A dermoscopy image of a single skin lesion: 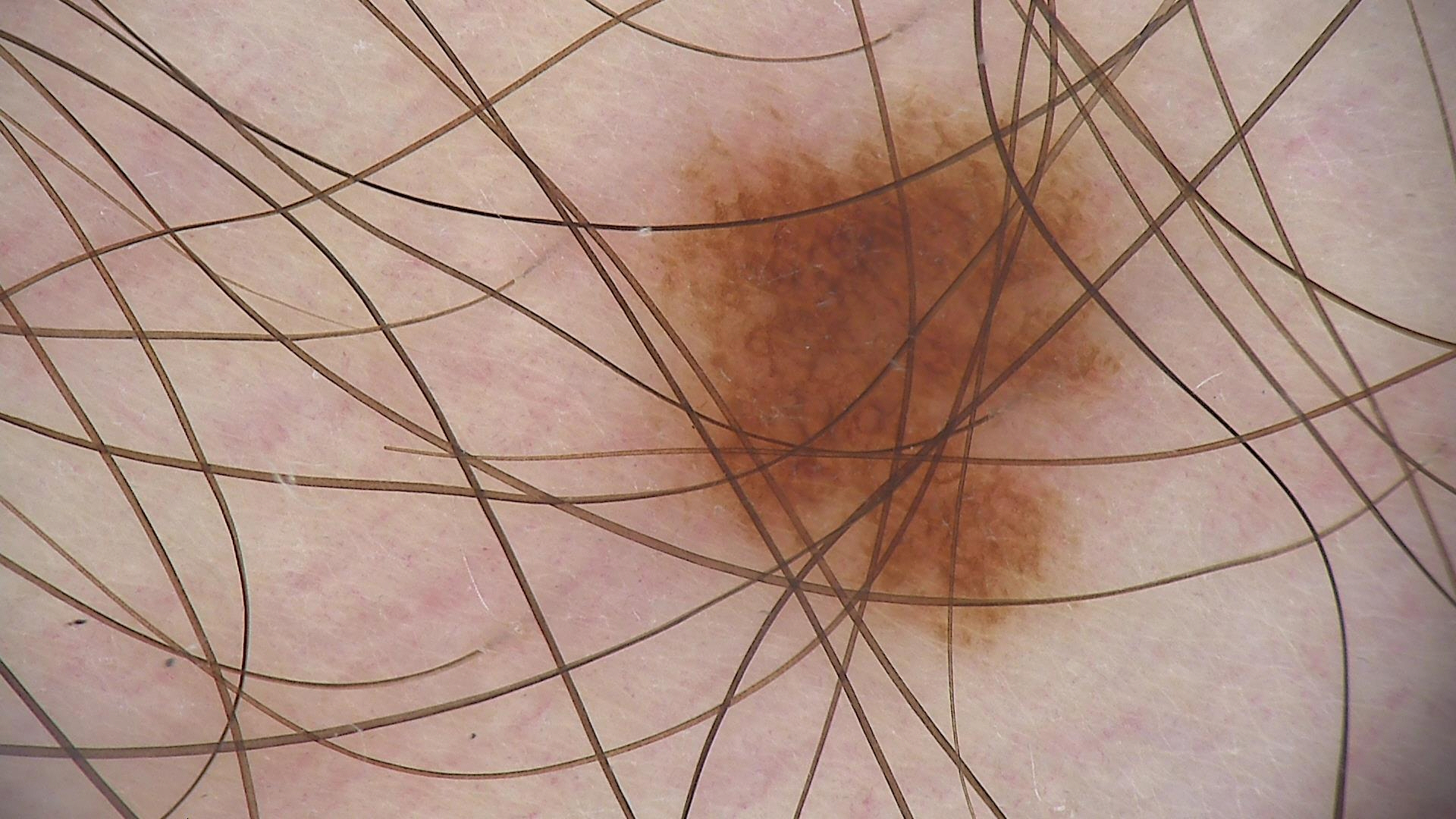diagnostic label: dysplastic junctional nevus (expert consensus).